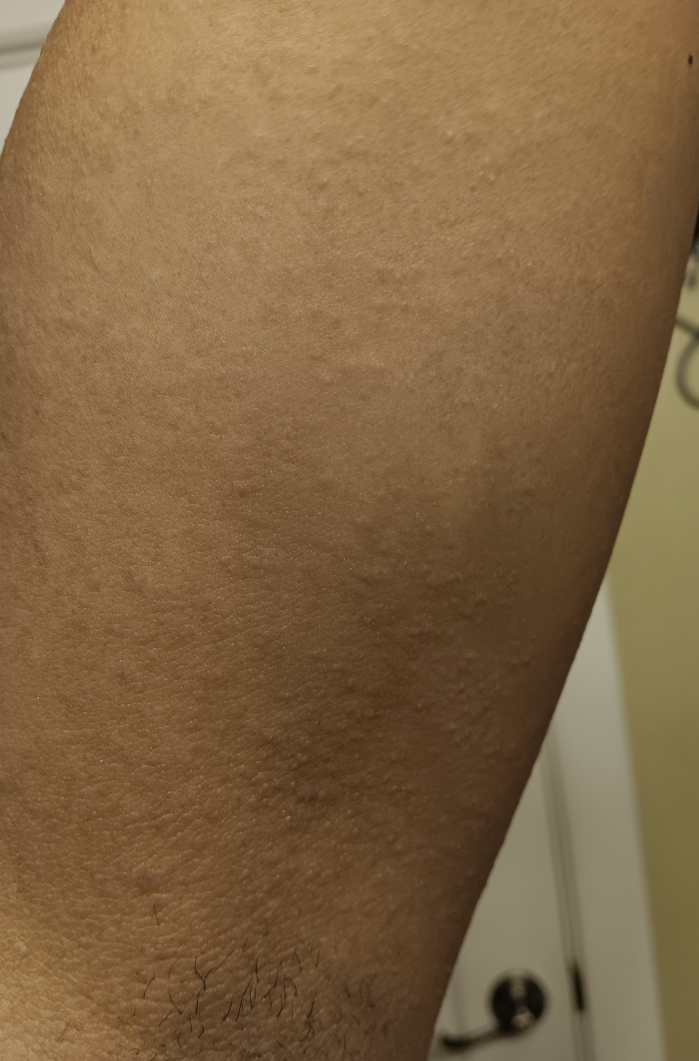Case summary:
* assessment · indeterminate
* texture · raised or bumpy
* location · leg, head or neck and arm
* patient describes the issue as · acne
* lesion symptoms · itching and burning
* history · one to four weeks
* framing · at an angle